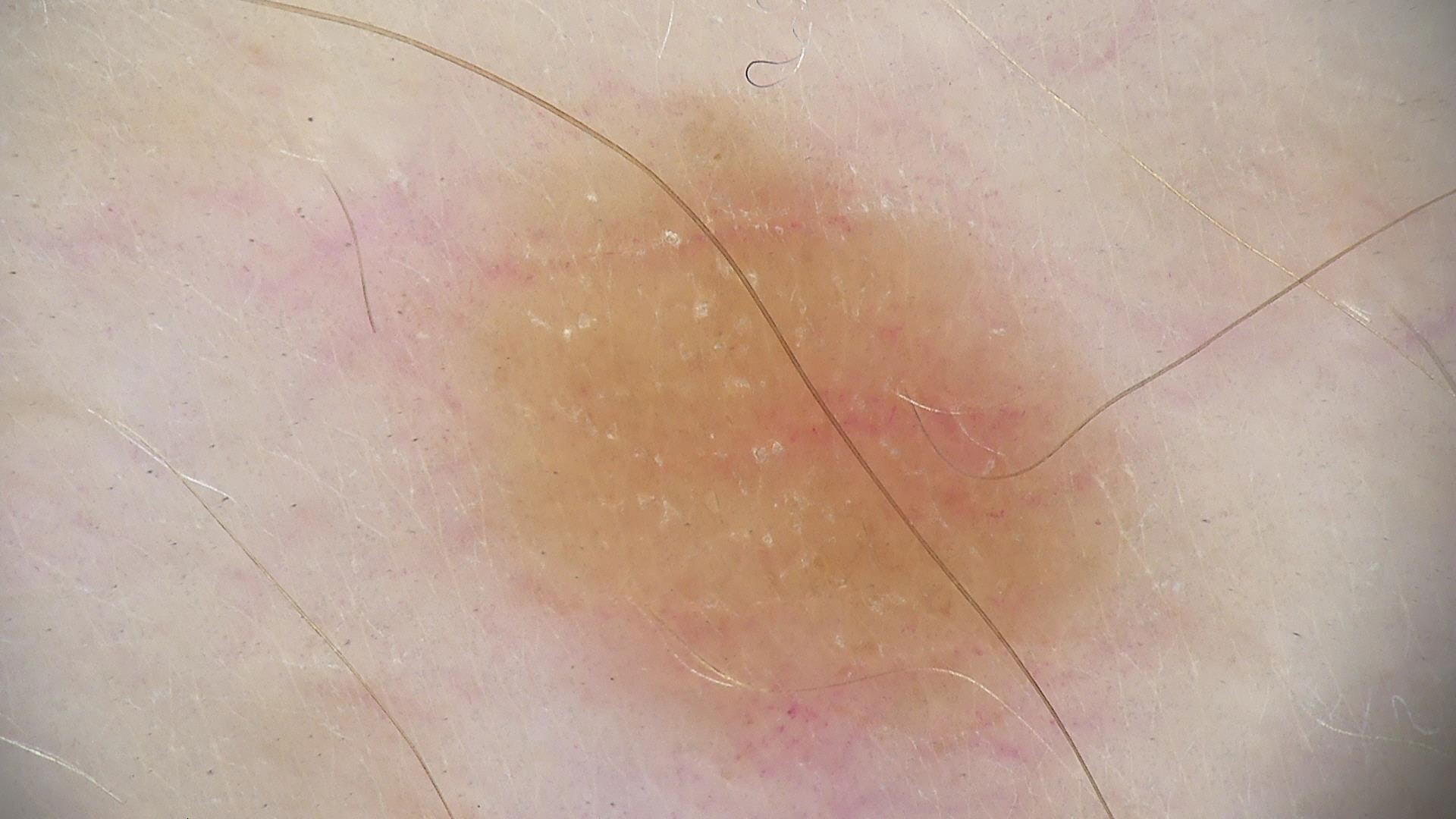The diagnostic label was a dysplastic junctional nevus.